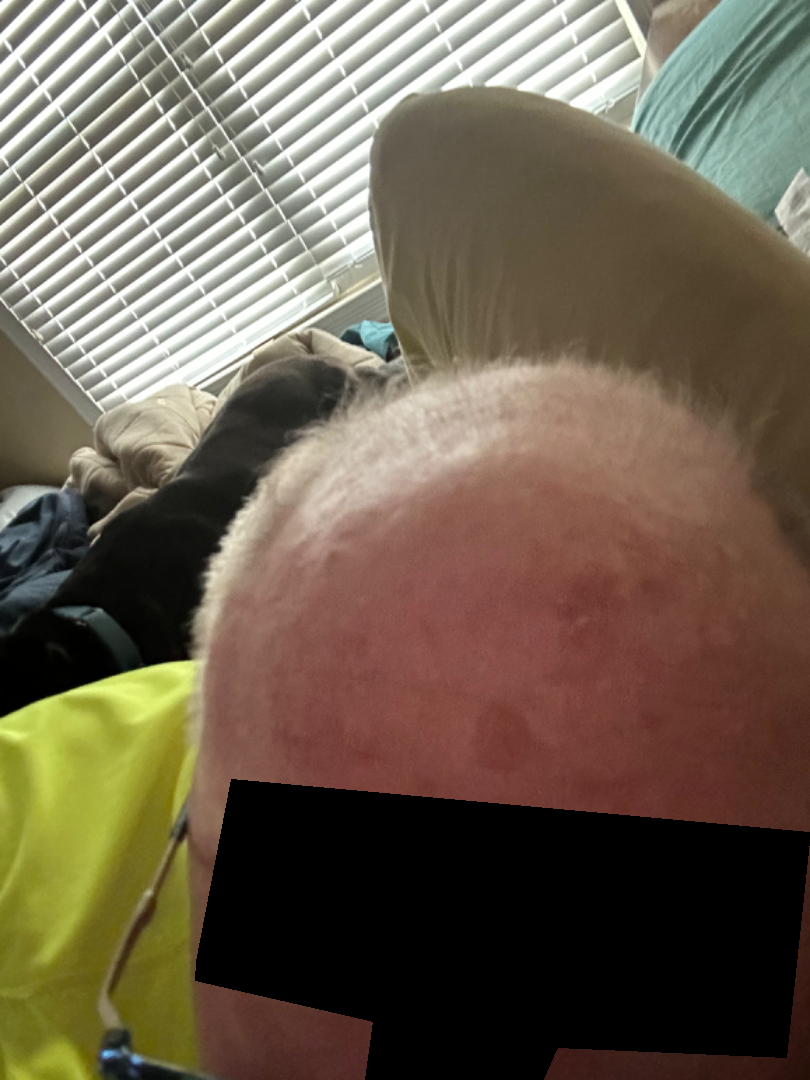The dermatologist could not determine a likely condition from the photograph alone. No associated systemic symptoms reported. Present for one to three months. Symptoms reported: burning, bleeding, bothersome appearance and pain. The lesion involves the head or neck. The photograph was taken at an angle. Texture is reported as rough or flaky. The patient described the issue as a rash.